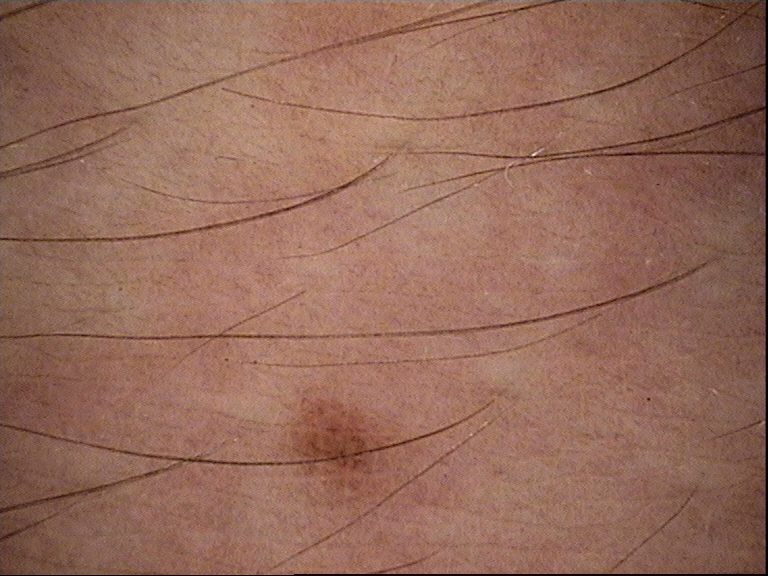The morphology is that of a banal lesion.
The diagnosis was a junctional nevus.